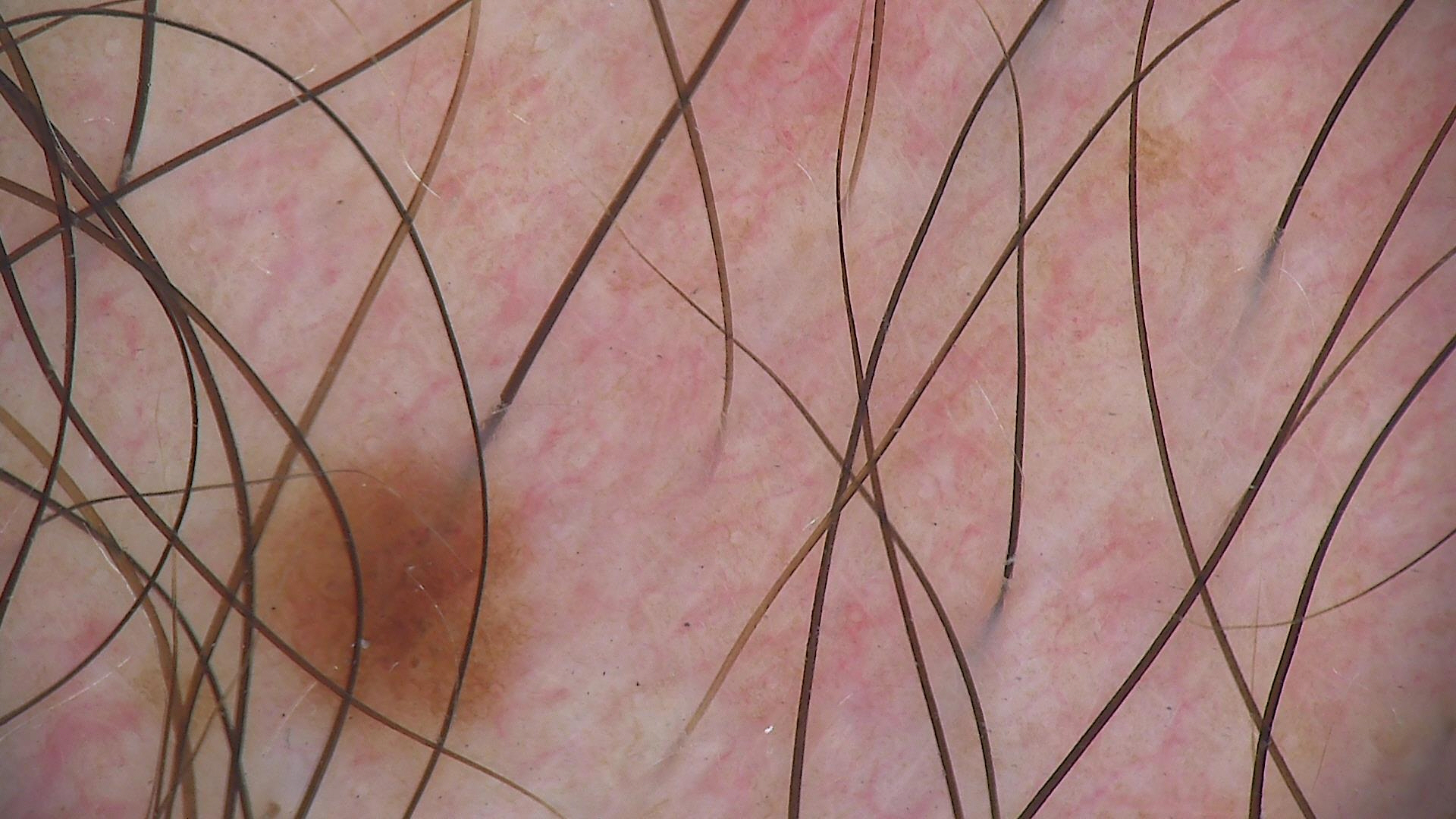A dermoscopic image of a skin lesion.
Diagnosed as a benign lesion — a dysplastic junctional nevus.